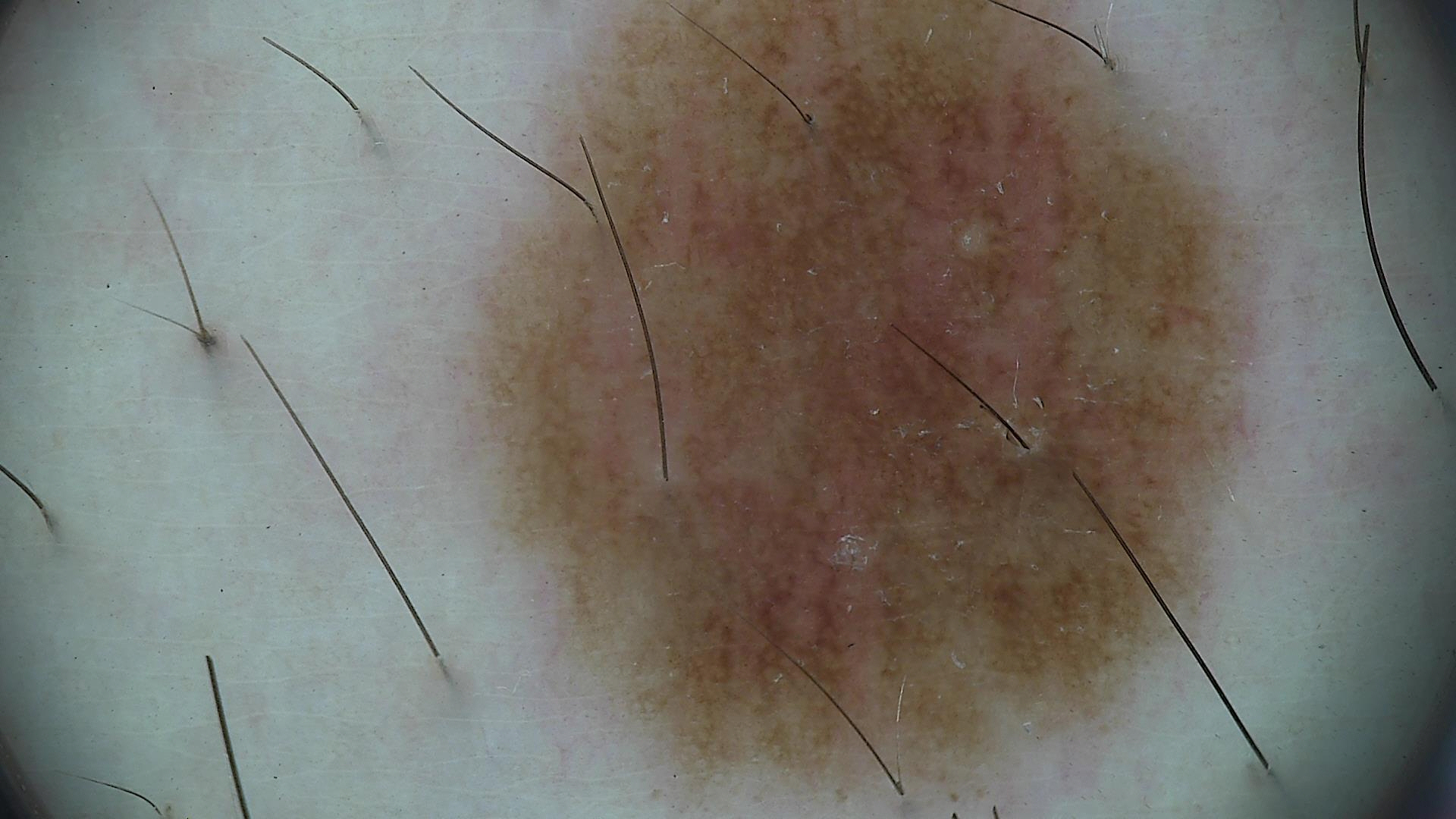Conclusion:
Diagnosed as a dysplastic junctional nevus.